This is a close-up image — 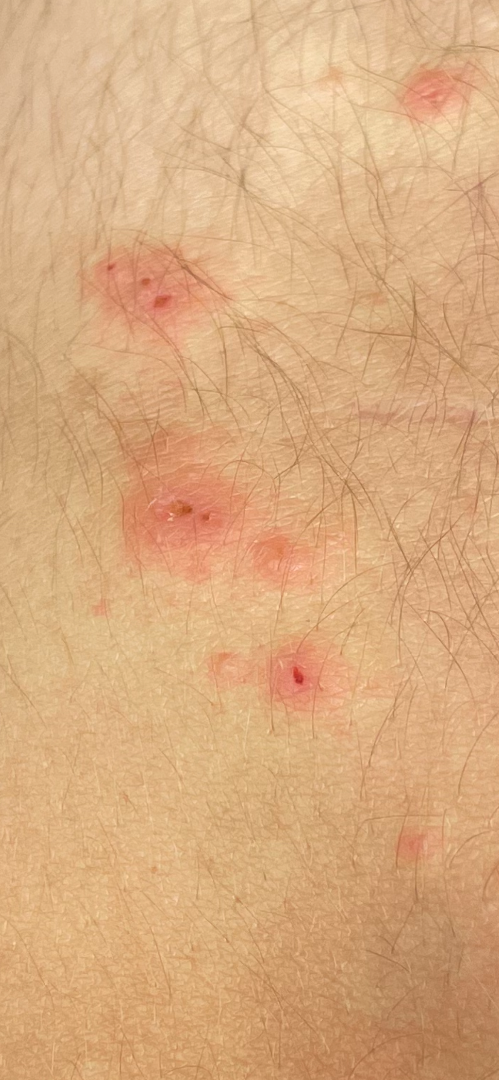The reviewer was unable to grade this case for skin condition.